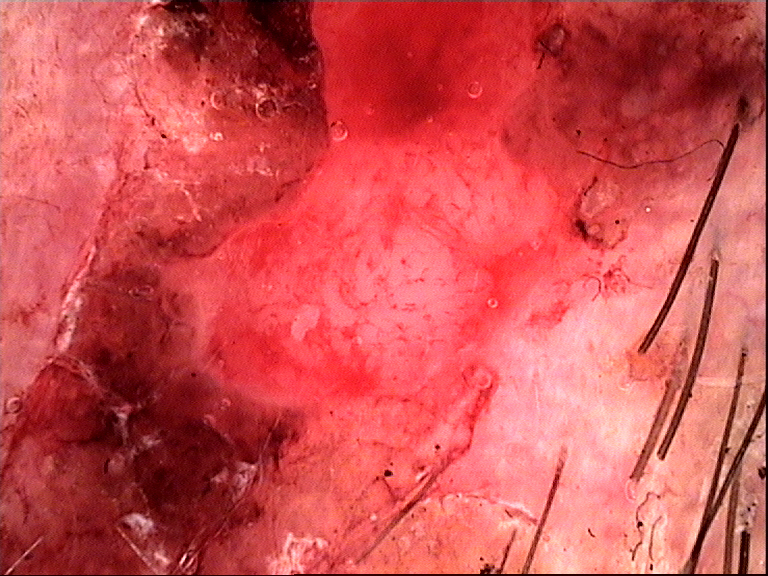Confirmed on histopathology as a squamous cell carcinoma.